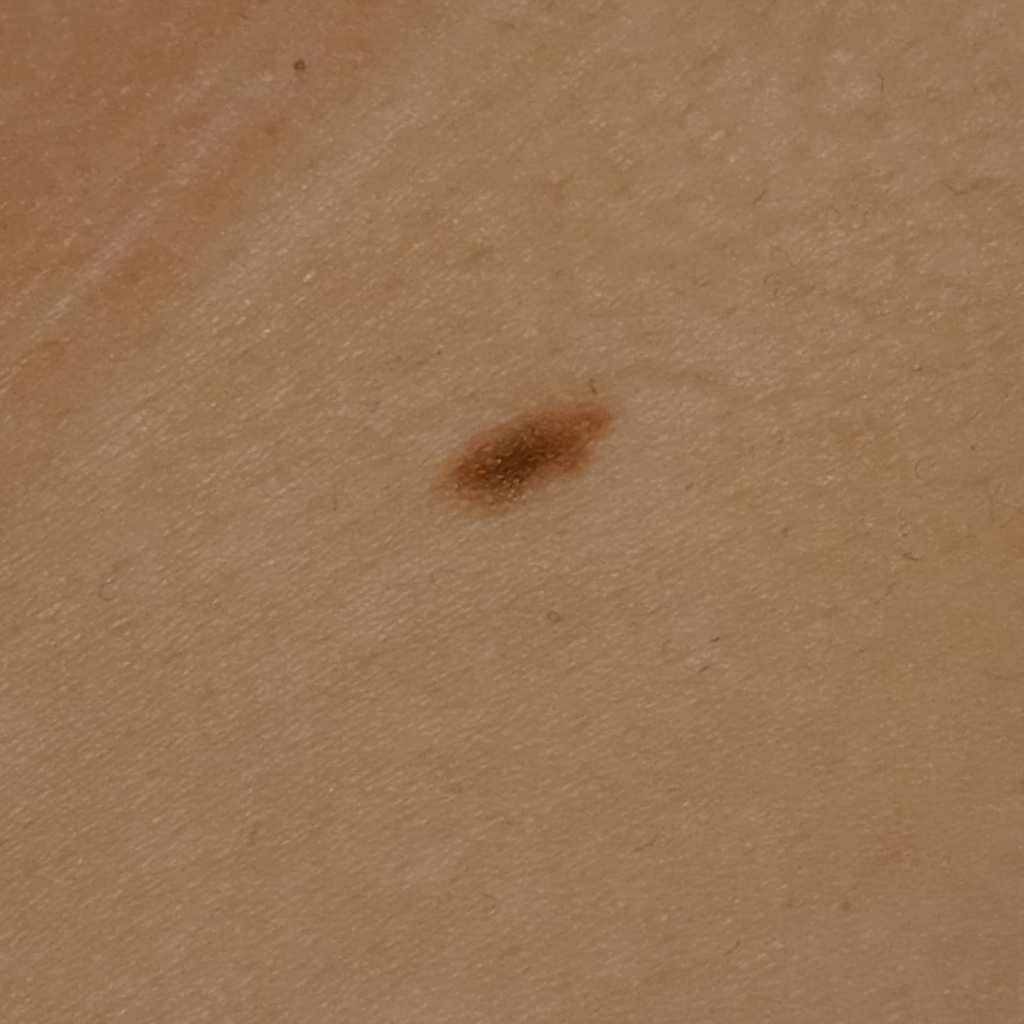{"image": "clinical photo", "patient": {"age": 35, "sex": "female"}, "sun_reaction": "skin reddens painfully with sun exposure", "lesion_location": "the torso", "diagnosis": {"name": "melanocytic nevus", "malignancy": "benign"}}